An image taken at an angle; the subject is a female aged 18–29:
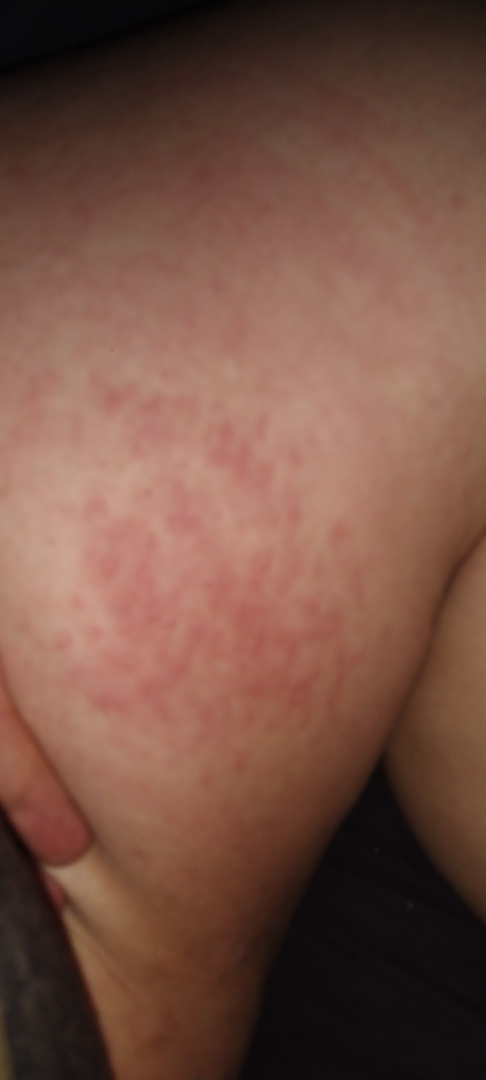Q: Reported symptoms?
A: itching and enlargement
Q: Constitutional symptoms?
A: none reported
Q: How long has this been present?
A: more than one year
Q: What is the dermatologist's impression?
A: Eczema, Allergic Contact Dermatitis and Irritant Contact Dermatitis were each considered, in no particular order